A clinical photograph of a skin lesion · a patient 62 years old — 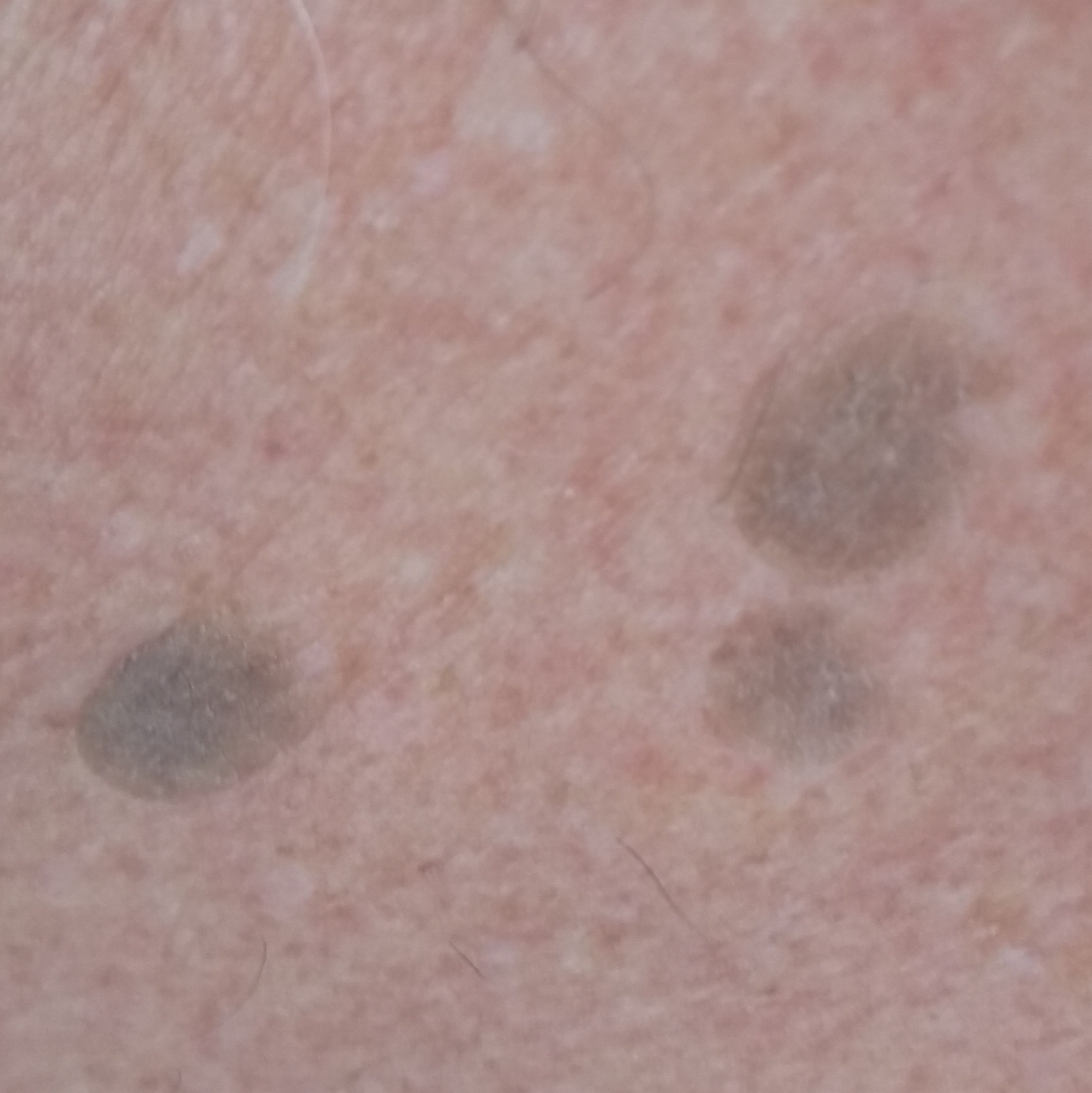Findings:
* location: the back
* diagnostic label: seborrheic keratosis (clinical consensus)